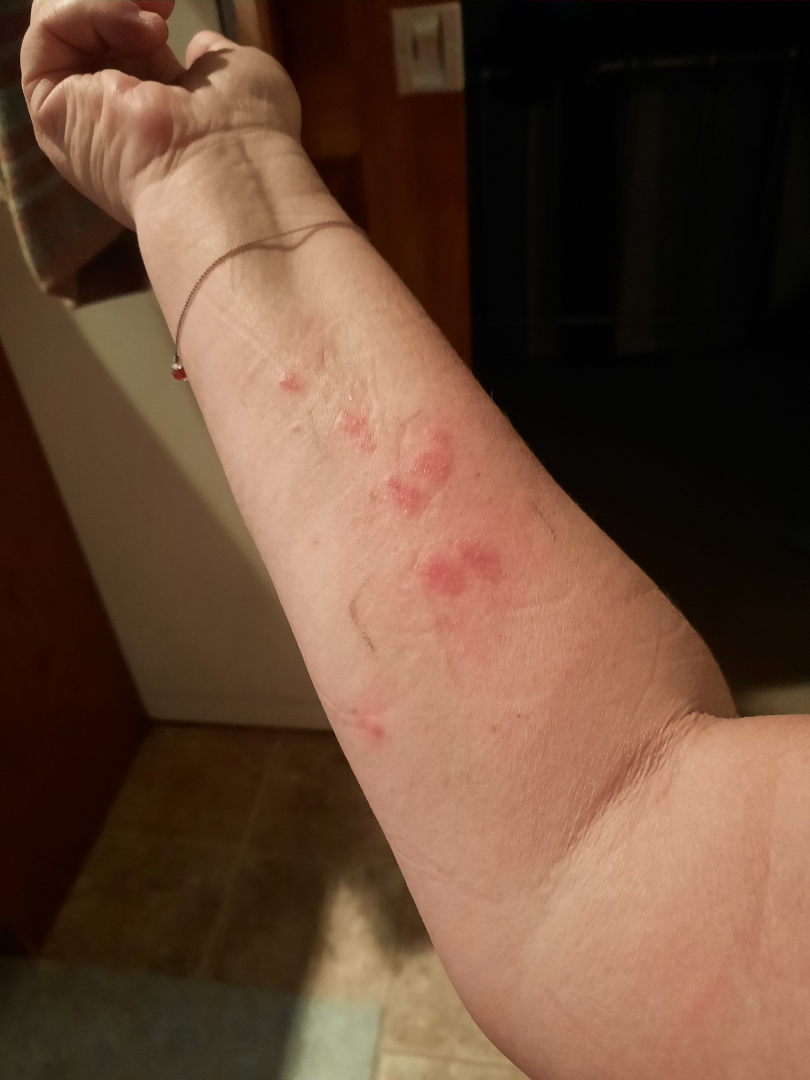Background:
An image taken at a distance. The leg, arm and front of the torso are involved.
Findings:
The reviewing clinician's impression was: Psoriasis (0.33); Eczema (0.33); Allergic Contact Dermatitis (0.33).